Present for about one day; no constitutional symptoms were reported; the affected area is the arm; no relevant lesion symptoms reported; the photo was captured at a distance; self-categorized by the patient as a rash:
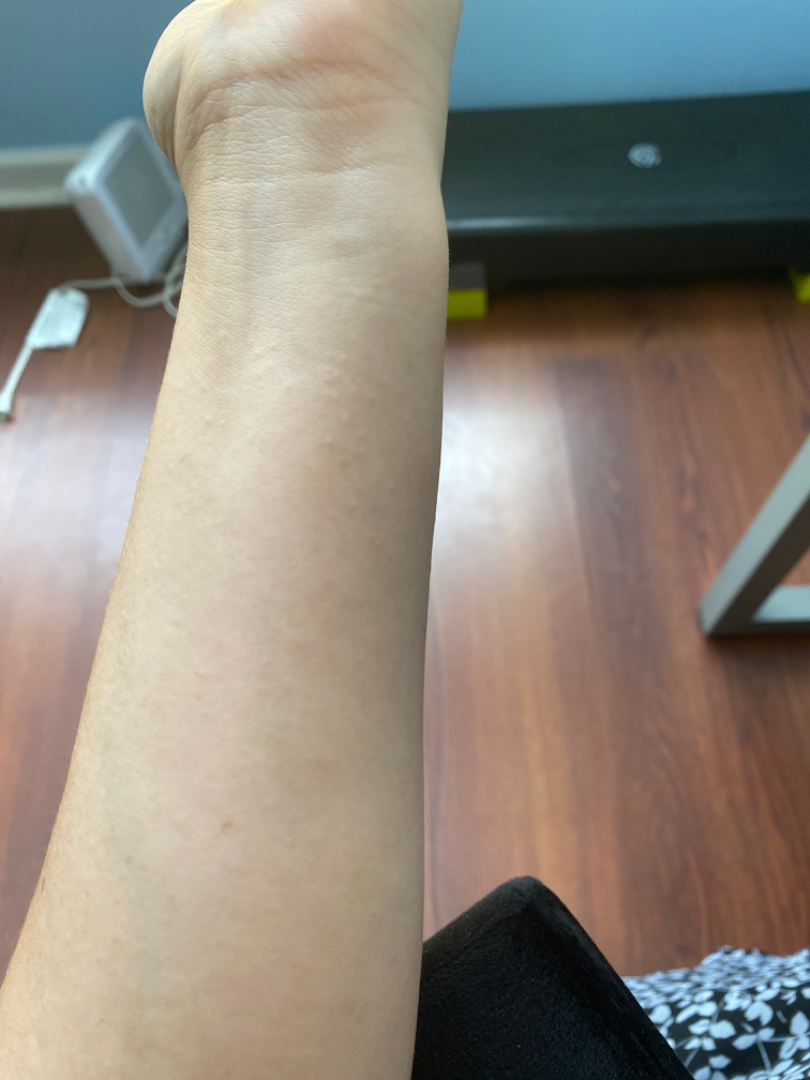The skin condition could not be confidently assessed from this image.